The patient considered this skin that appeared healthy to them · the top or side of the foot is involved · the condition has been present for one to four weeks · the photograph was taken at a distance · the patient indicates the lesion is raised or bumpy and rough or flaky · no relevant systemic symptoms.
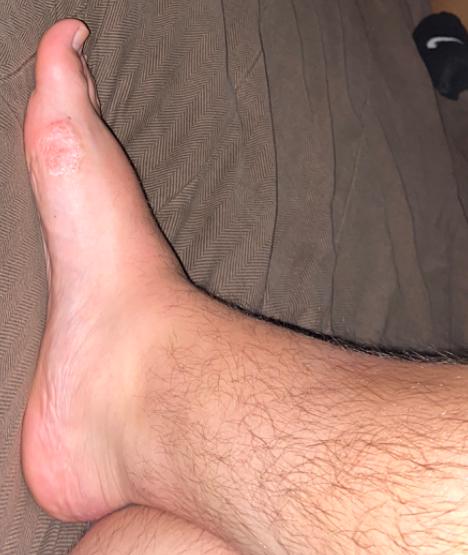The case was difficult to assess from the available photograph.